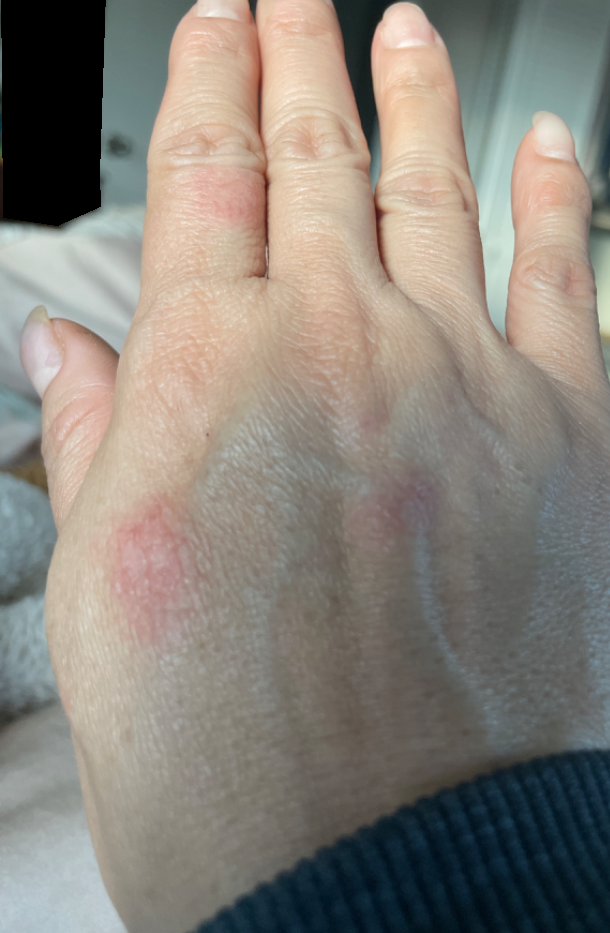The back of the hand is involved.
The patient considered this a rash.
Texture is reported as rough or flaky.
The contributor reports associated fatigue and joint pain.
This image was taken at an angle.
Skin tone: Fitzpatrick phototype II; lay reviewers estimated Monk Skin Tone 7 (US pool) or 2 (India pool).
On dermatologist assessment of the image, Prurigo nodularis (possible); Eczema (possible); Insect Bite (less likely); Lichen Simplex Chronicus (less likely); Keratosis (less likely).